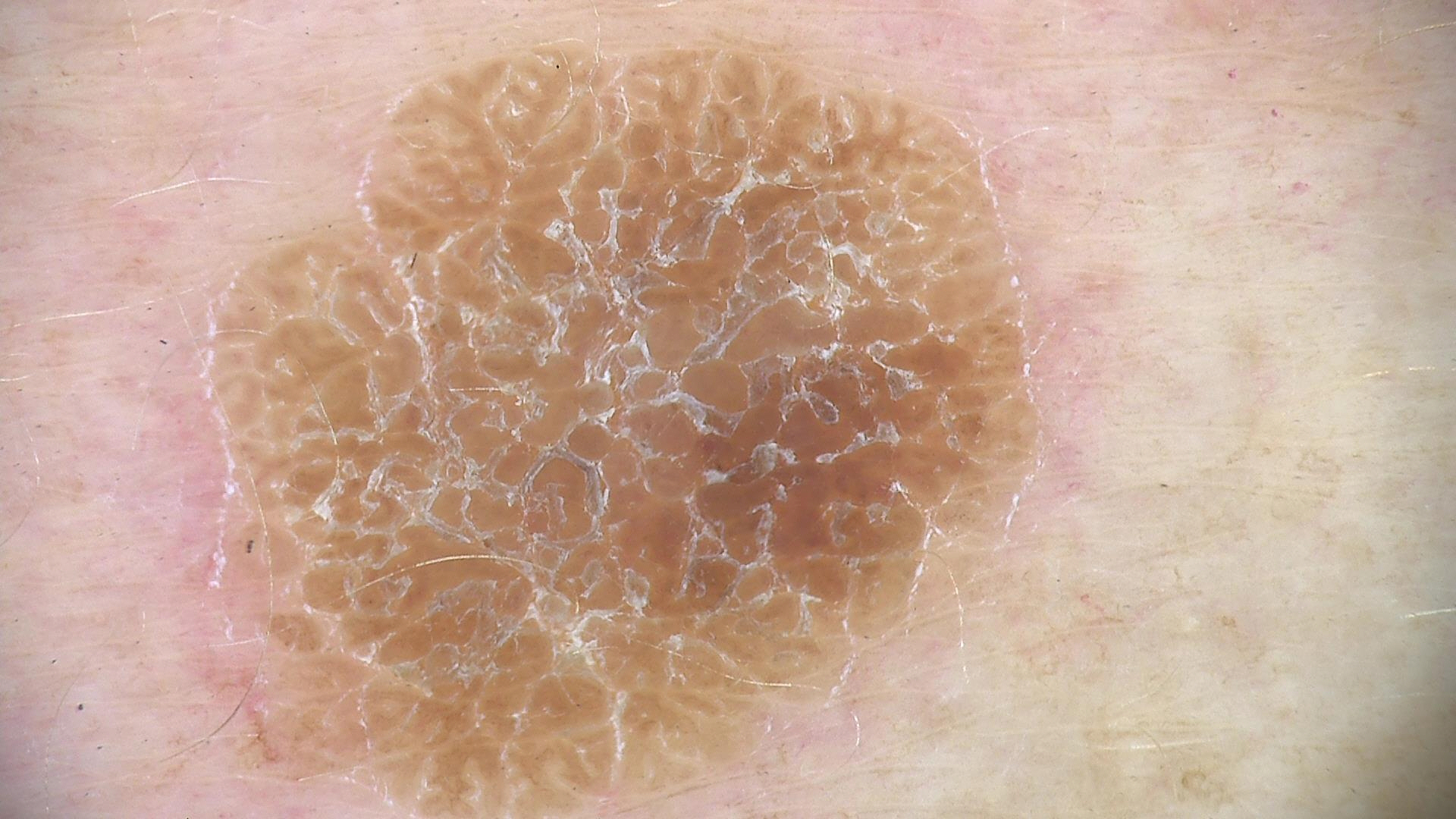Q: What is the lesion category?
A: keratinocytic
Q: What was the diagnostic impression?
A: seborrheic keratosis (expert consensus)